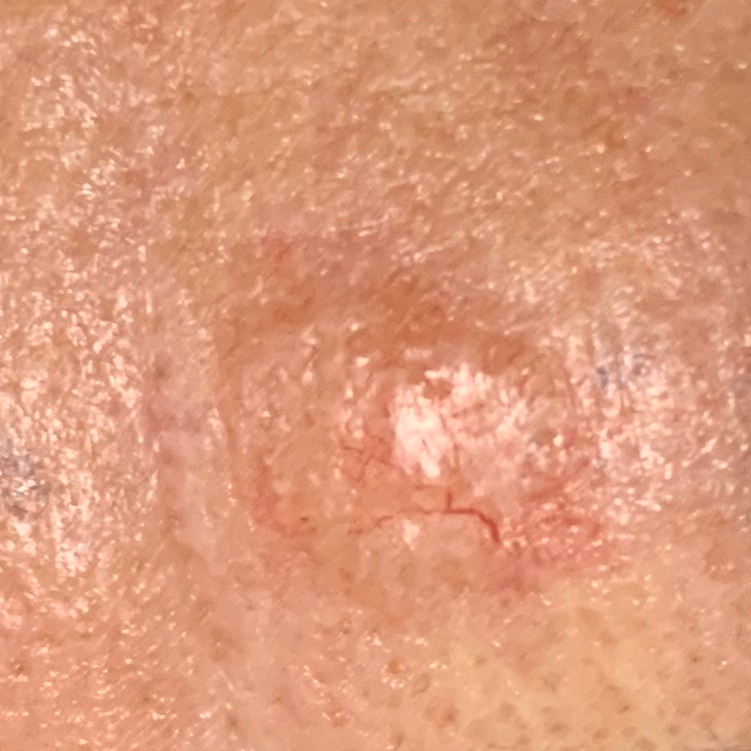A female subject age 64.
The lesion is located on the face.
The lesion is roughly 7 by 7 mm.
Per patient report, the lesion is elevated.
Histopathology confirmed a malignant skin lesion — a basal cell carcinoma.